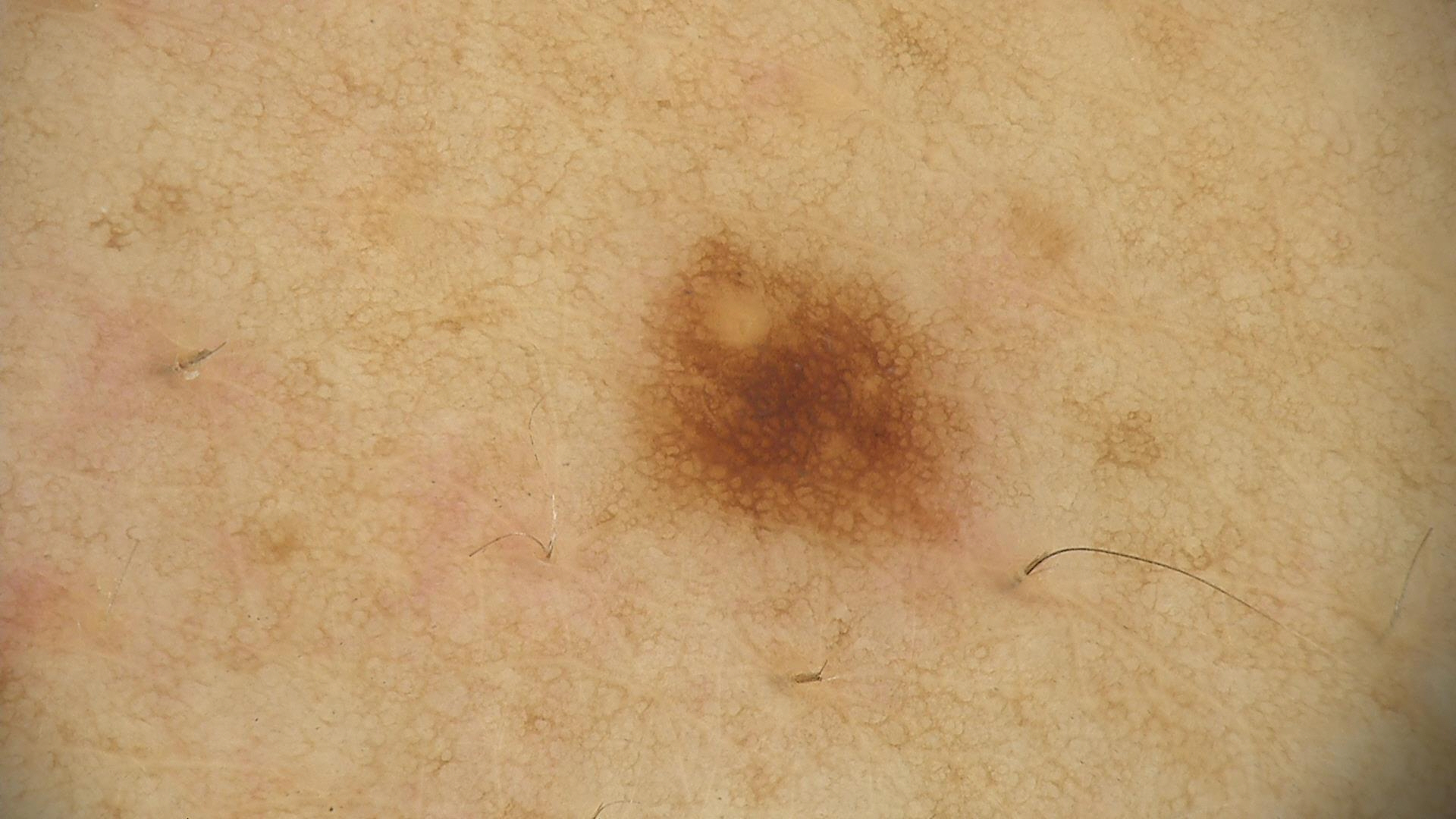imaging: dermatoscopy | assessment: dysplastic junctional nevus (expert consensus).